This is a close-up image, the affected area is the leg:
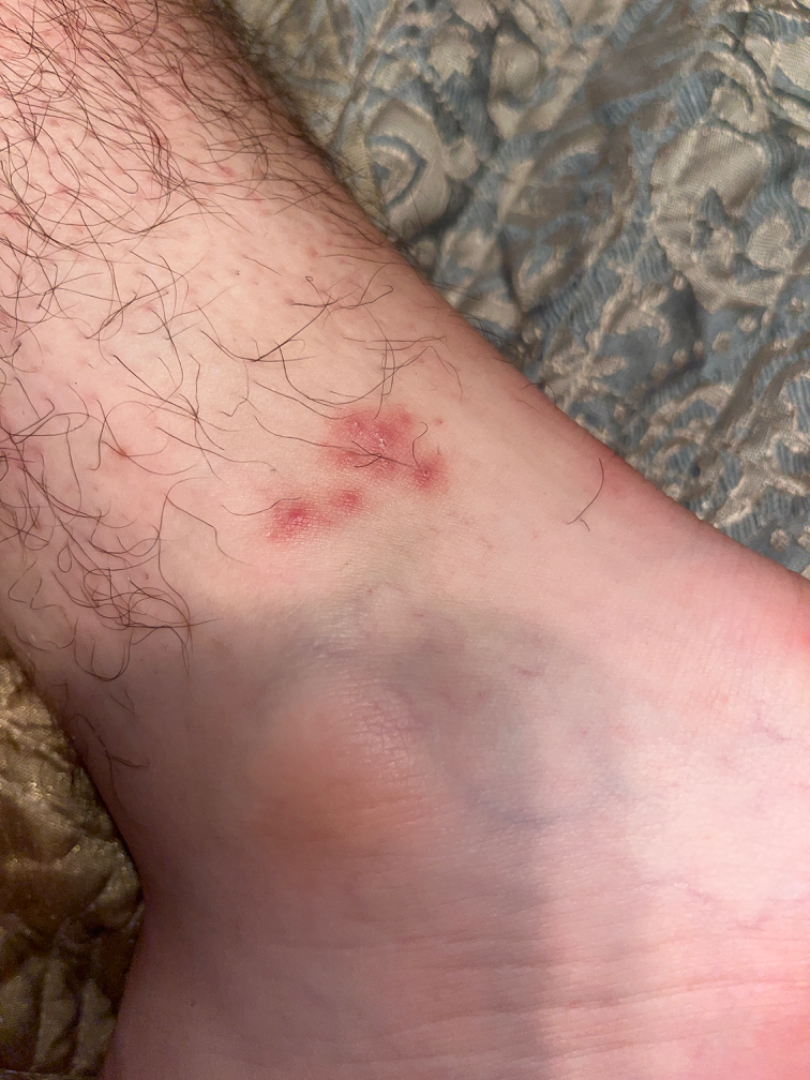Case summary:
– clinical impression · Pigmented purpuric eruption (considered); Allergic Contact Dermatitis (considered); Herpes Simplex (considered)